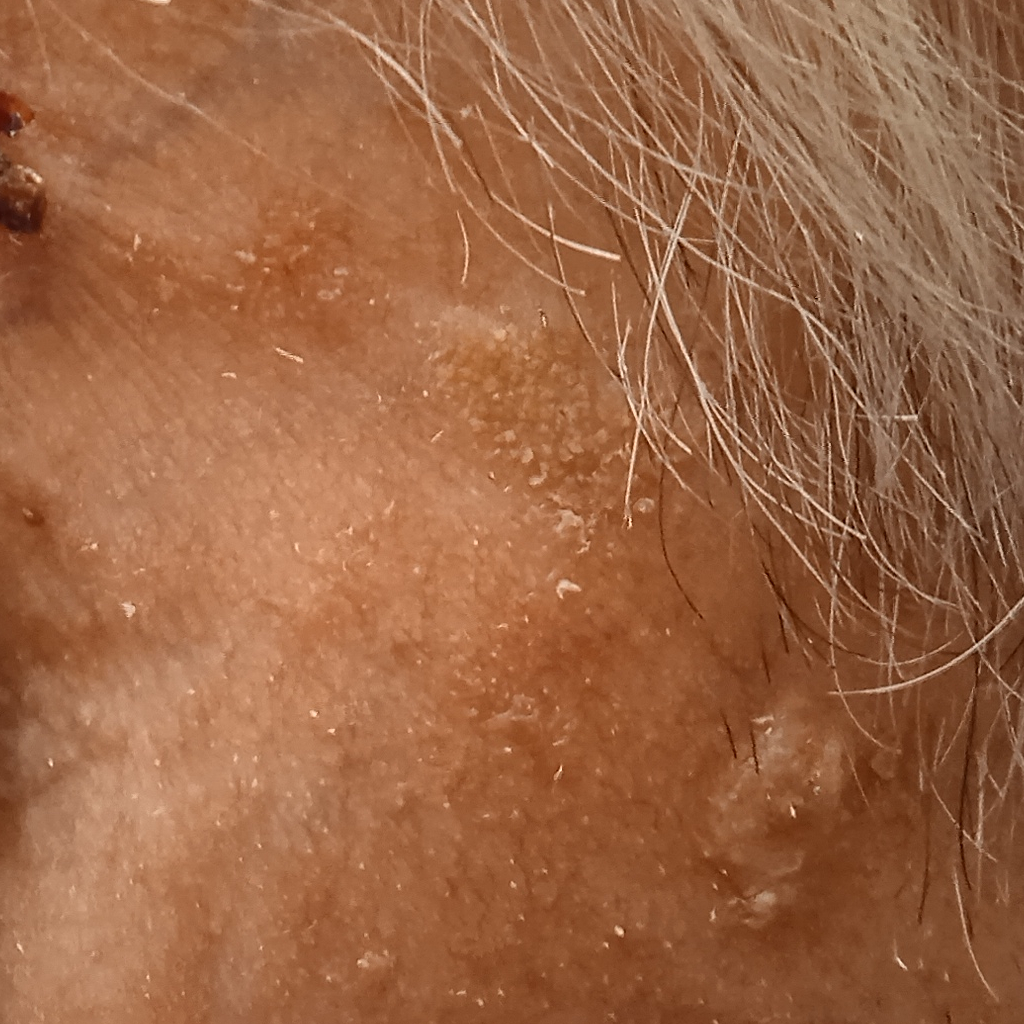{
  "image": "clinical photo",
  "referral": "research study (no referral diagnosis)",
  "patient": {
    "age": 89,
    "sex": "male"
  },
  "lesion_location": "the face",
  "lesion_size": {
    "diameter_mm": 8.8
  },
  "diagnosis": {
    "name": "seborrheic keratosis",
    "malignancy": "benign"
  }
}